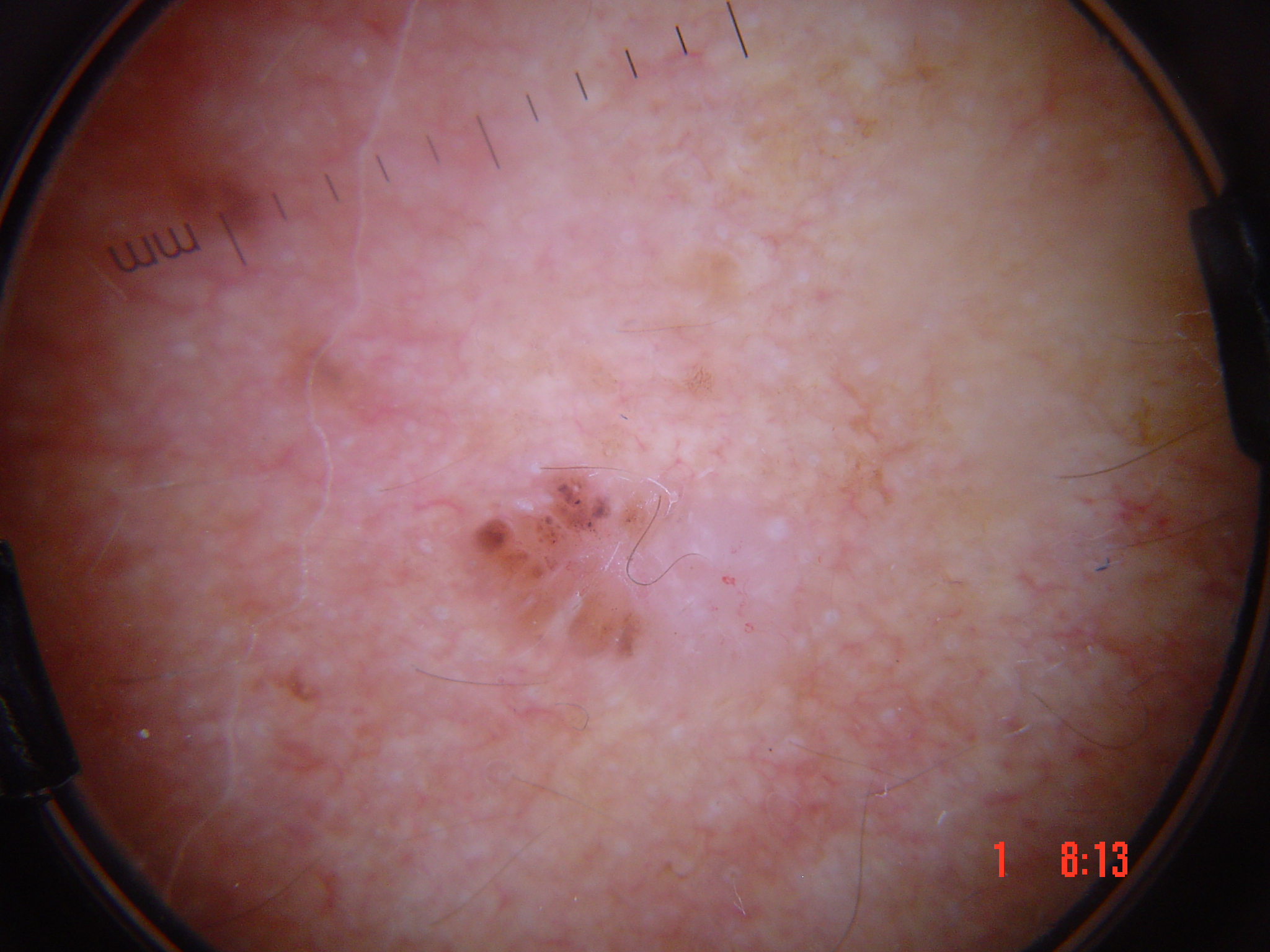Diagnosis:
Histopathology confirmed a basal cell carcinoma.